A female patient in their 80s · a skin lesion imaged with contact-polarized dermoscopy:
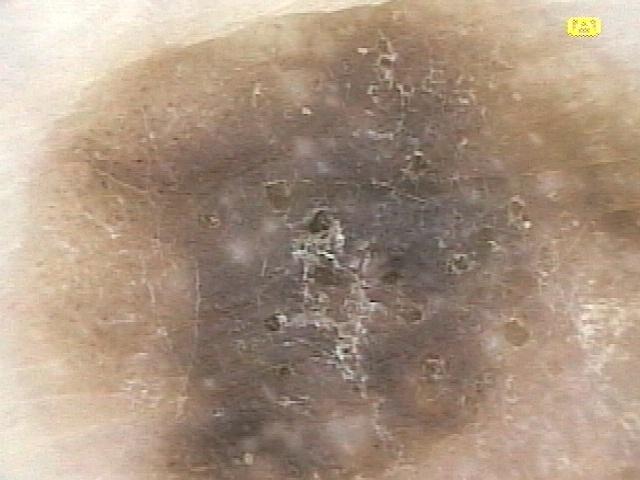Findings: The lesion is located on the trunk (the anterior trunk). Assessment: Expert review favored a lesion of epidermal origin — a seborrheic keratosis.